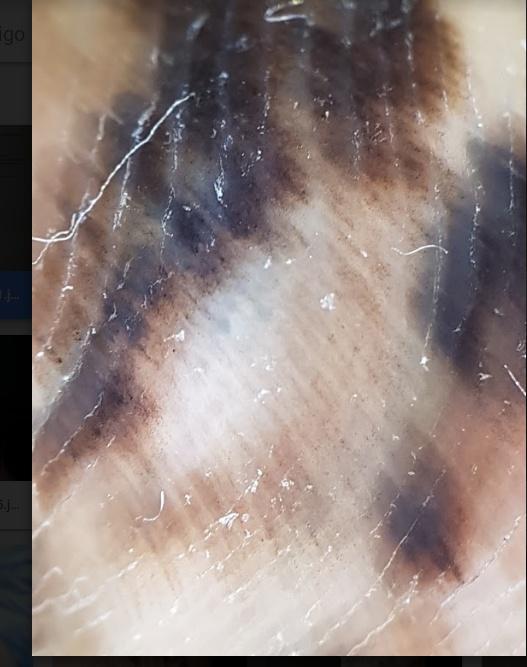<case>
  <diagnosis>
    <name>Melanoma</name>
    <malignancy>malignant</malignancy>
    <confirmation>histopathology</confirmation>
  </diagnosis>
</case>